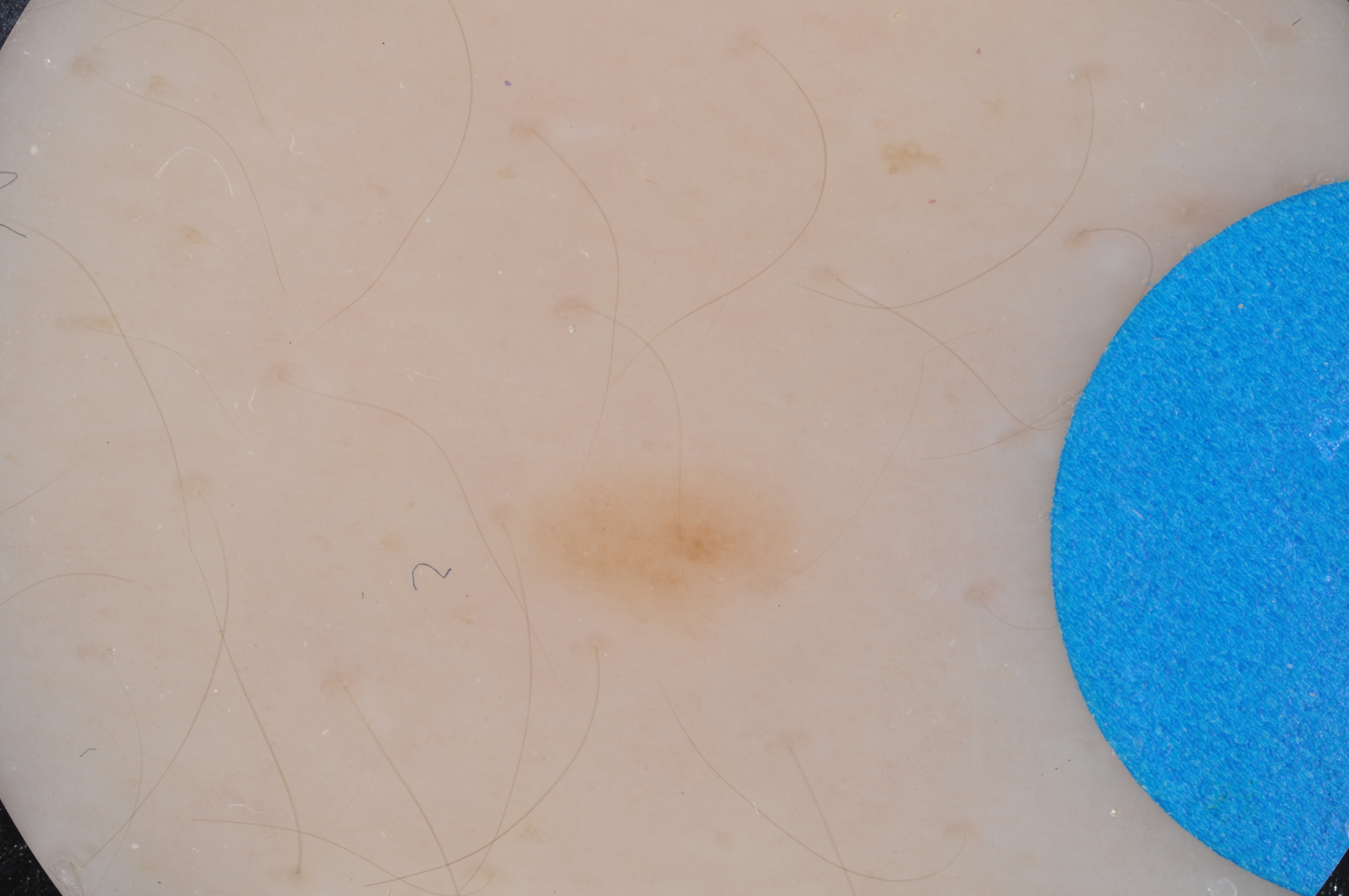Findings: A dermatoscopic image of a skin lesion. A male patient about 15 years old. With coordinates (x1, y1, x2, y2), the visible lesion spans bbox=[505, 462, 820, 627]. On dermoscopy, the lesion shows milia-like cysts, with no globules, pigment network, streaks, or negative network. Conclusion: The diagnostic assessment was a melanocytic nevus, a benign skin lesion.